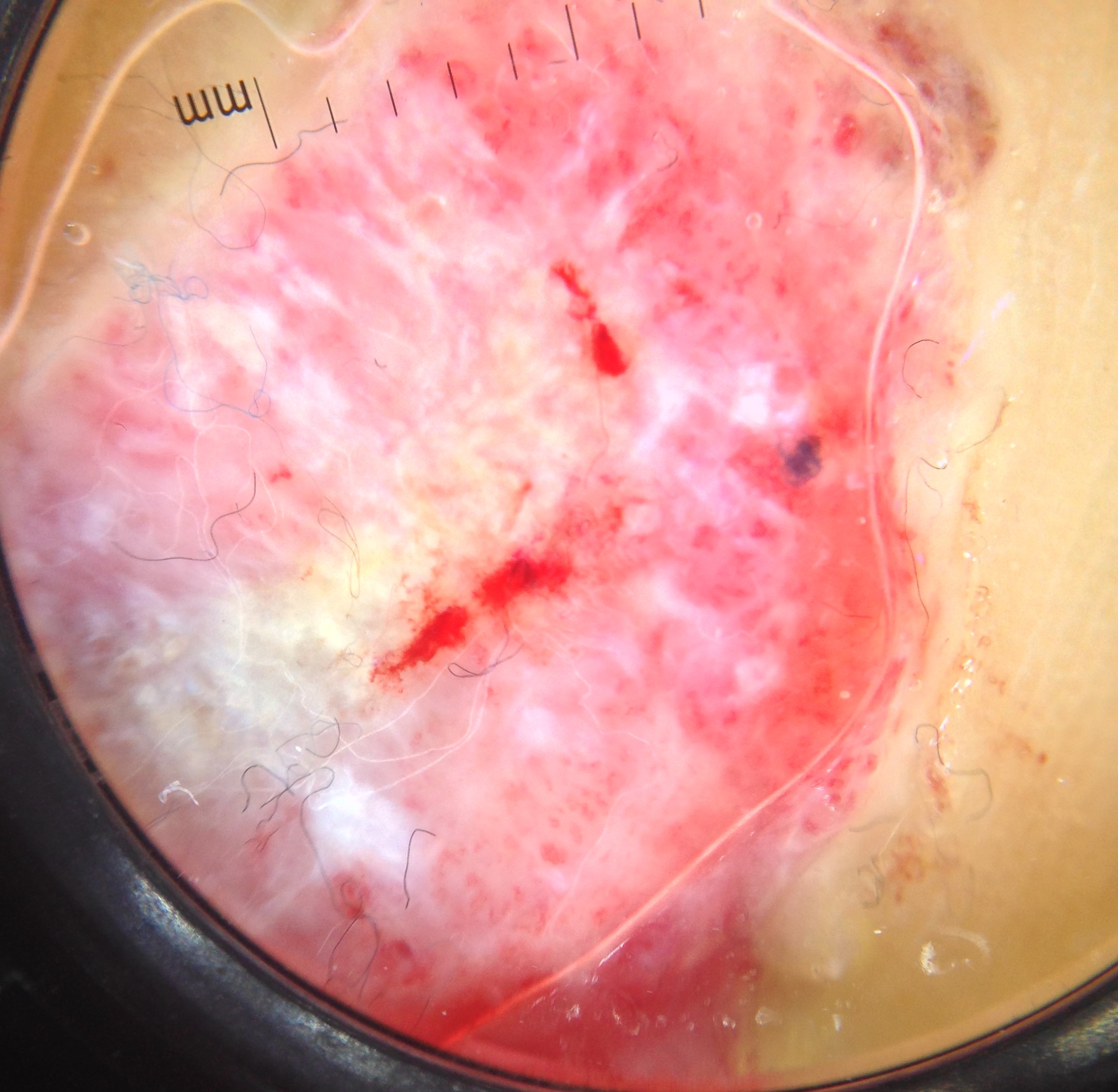Case: A dermatoscopic image of a skin lesion. Diagnosis: Biopsy-confirmed as a skin cancer — an acral nodular melanoma.